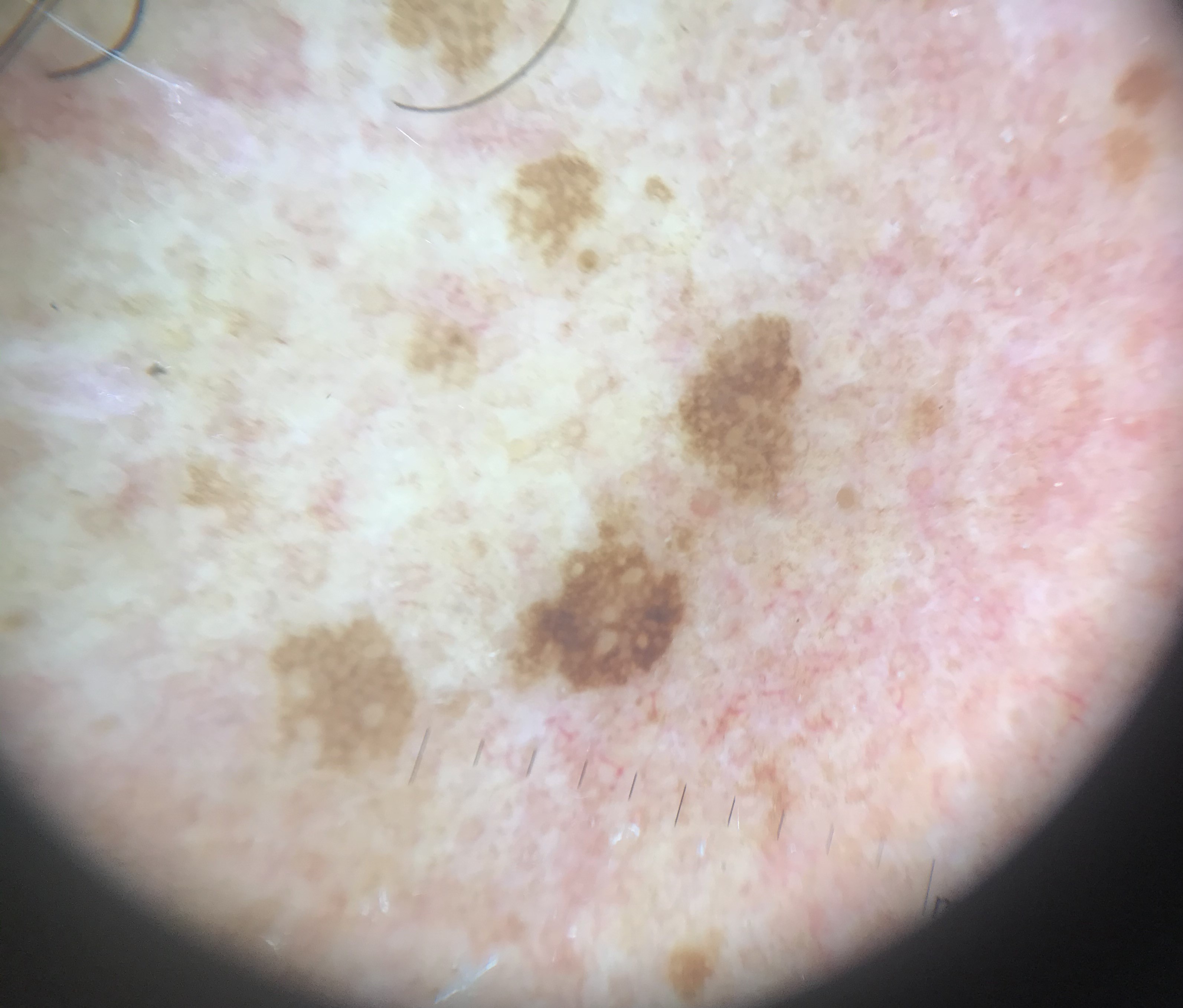Classified as a benign lesion — a seborrheic keratosis.